A clinical photograph of a skin lesion. A subject age 33.
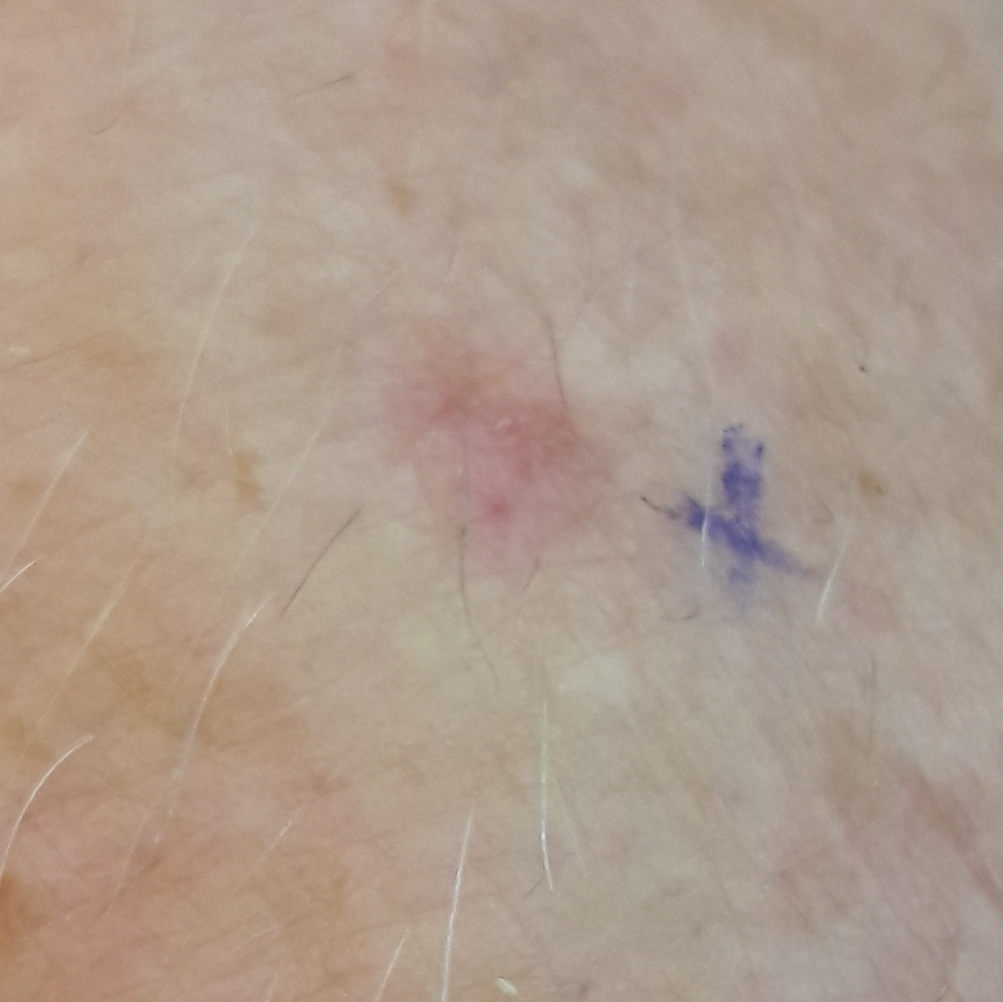Patient and lesion: The lesion was found on a hand. Conclusion: The consensus clinical diagnosis was an actinic keratosis.